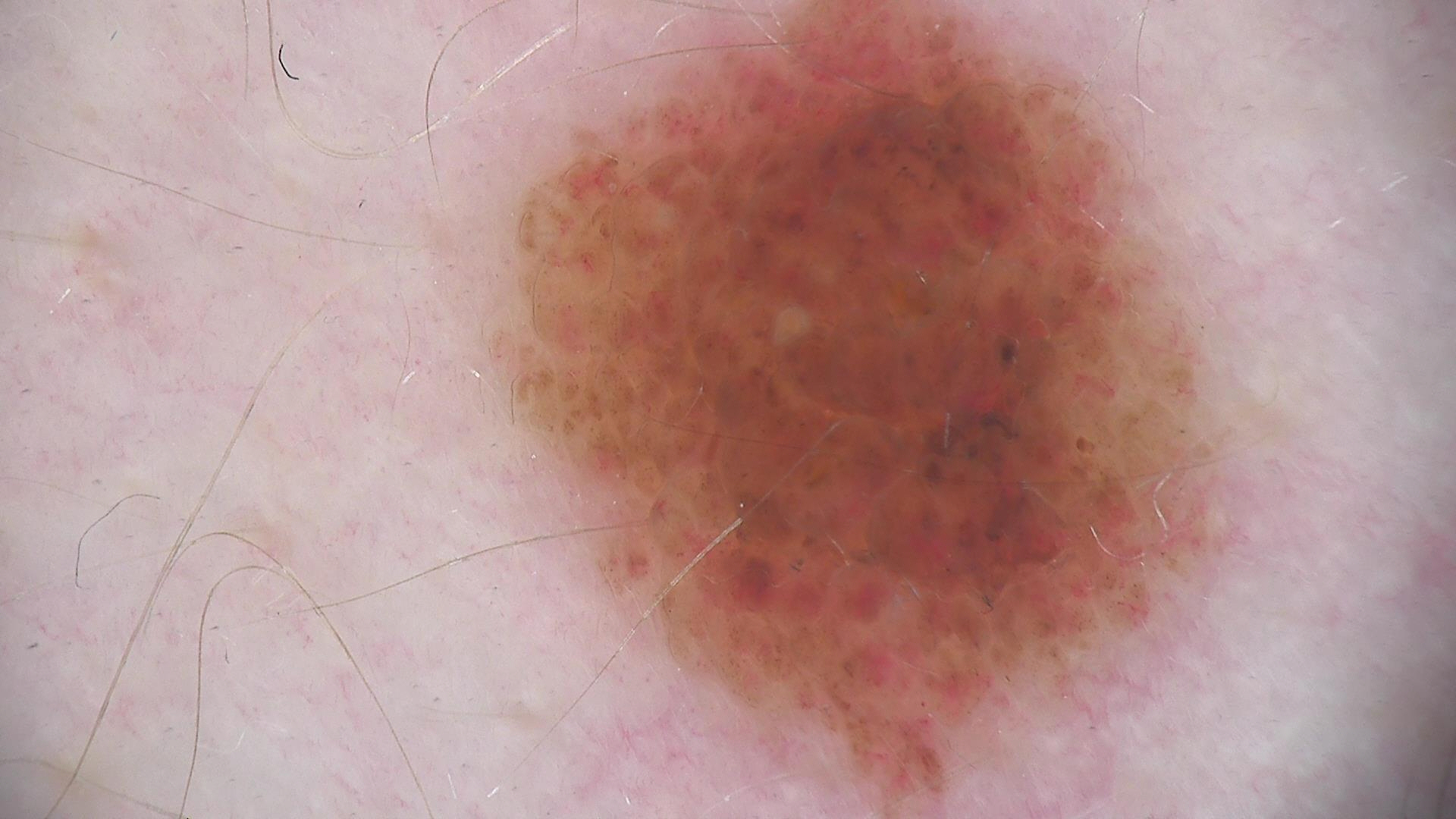Findings:
* label — compound nevus (expert consensus)